A dermatoscopic image of a skin lesion.
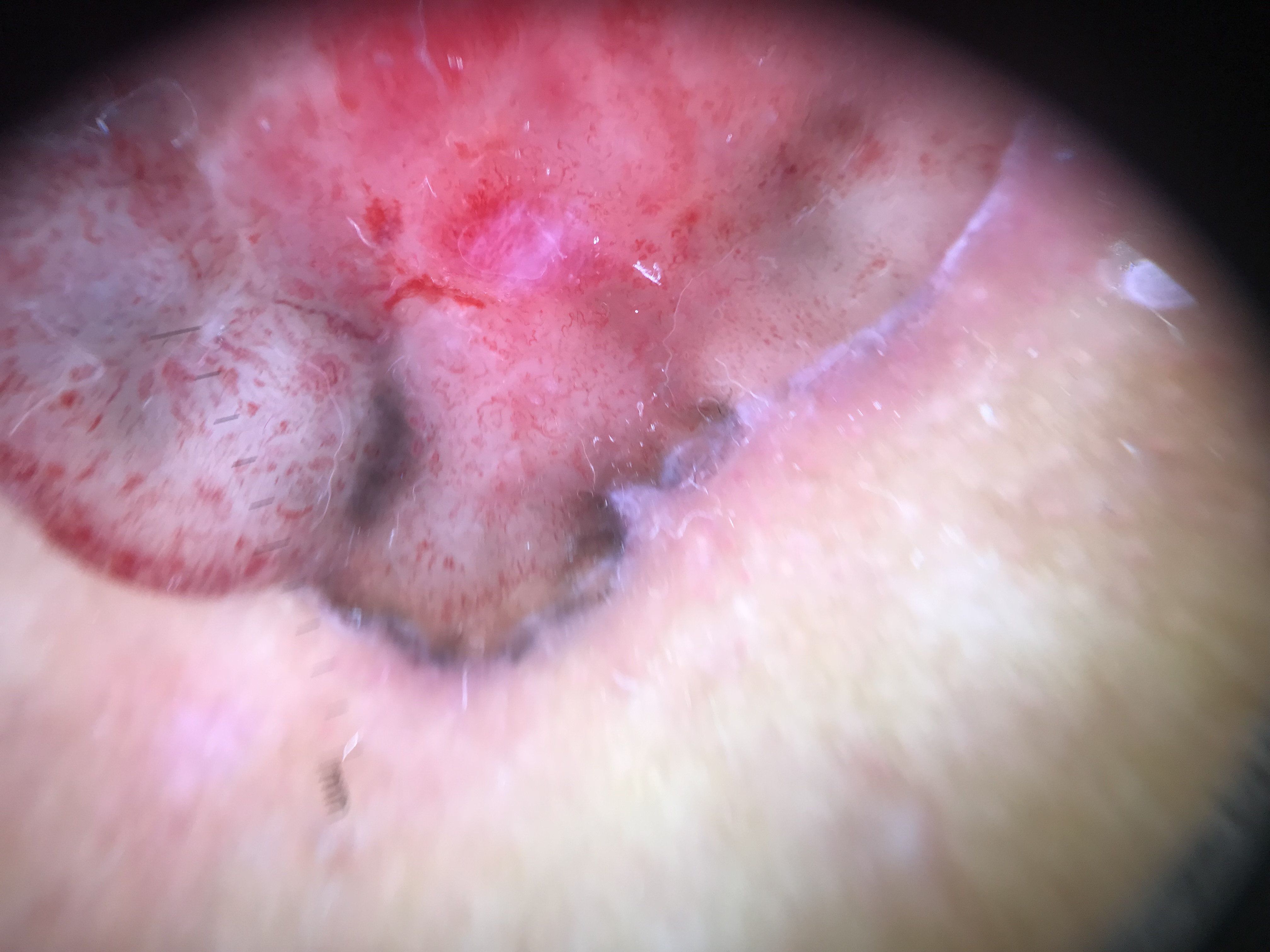pathology: basal cell carcinoma (biopsy-proven)